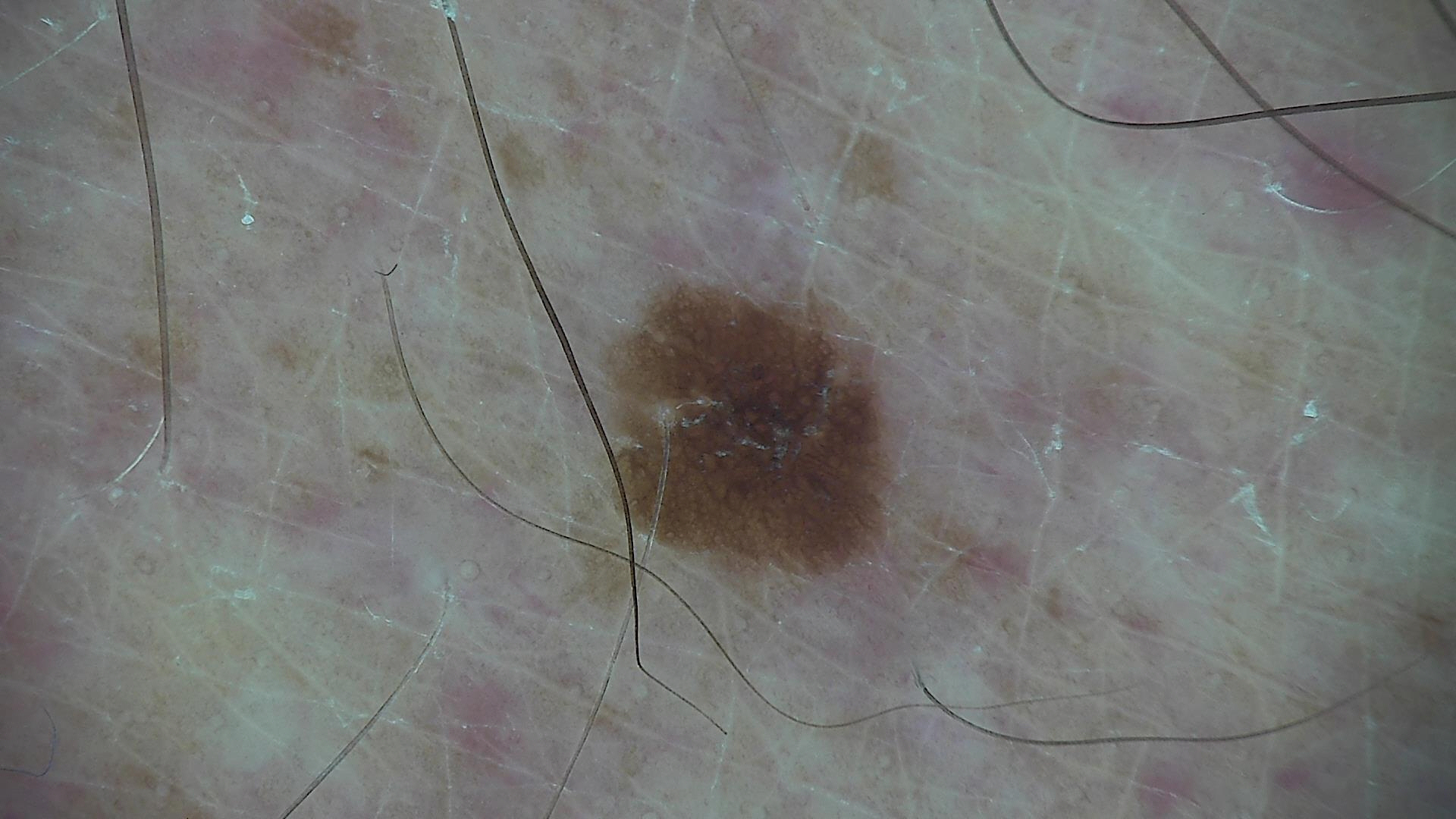label=dysplastic junctional nevus (expert consensus)